Reported duration is about one day. Male contributor, age 50–59. Texture is reported as raised or bumpy. No constitutional symptoms were reported. This is a close-up image. The head or neck is involved. Skin tone: Fitzpatrick skin type III; lay reviewers estimated MST 2 (US pool) or 3 (India pool).
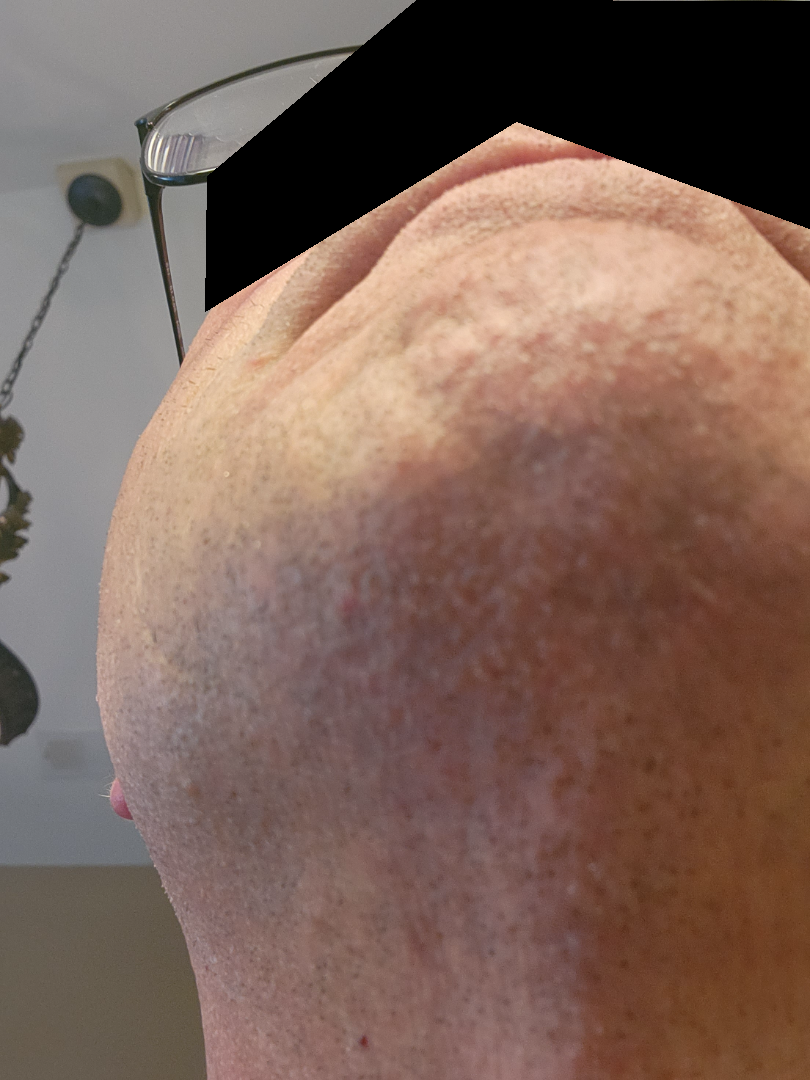The case was difficult to assess from the available photograph.